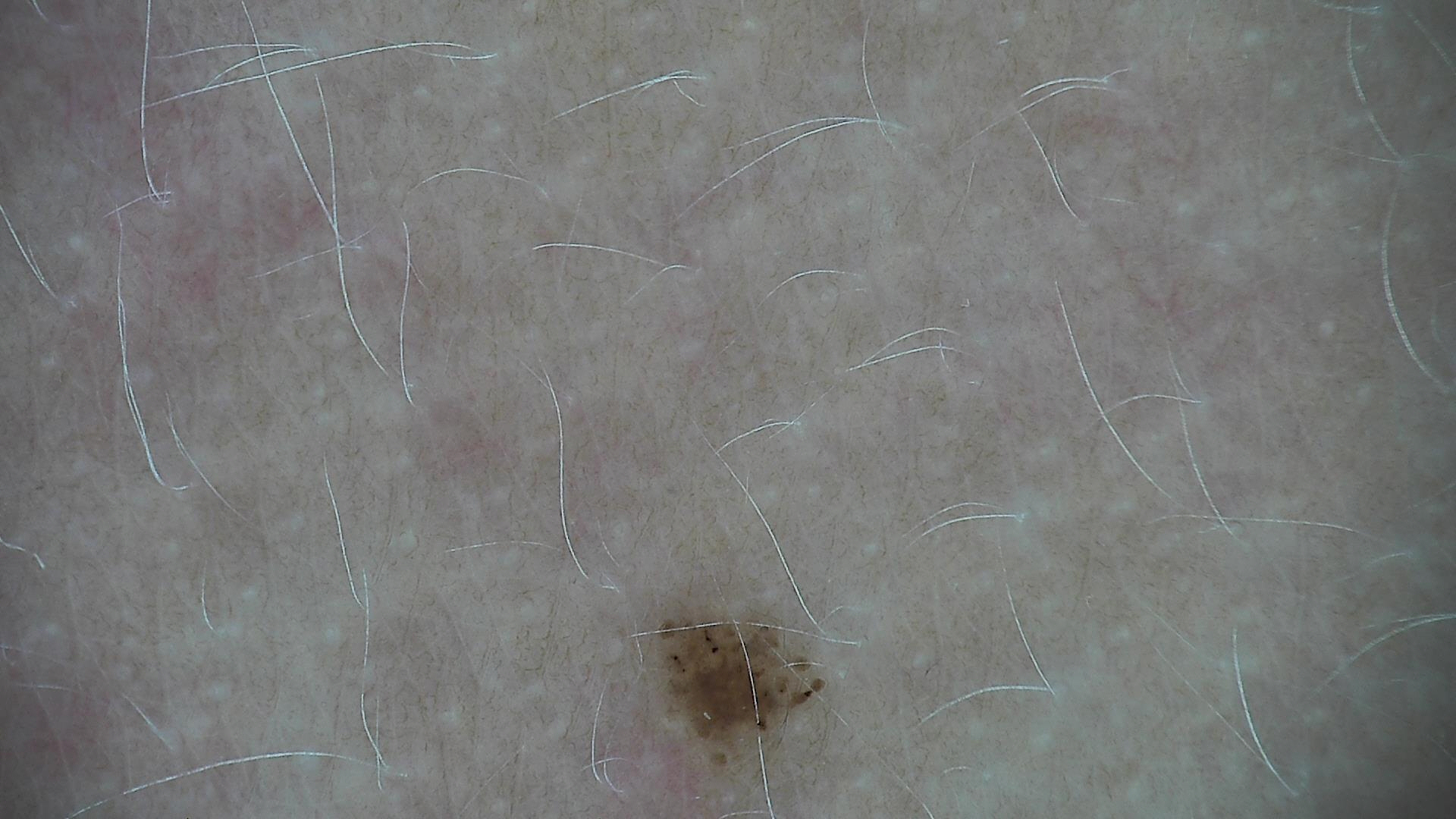modality = dermatoscopy | diagnostic label = dysplastic junctional nevus (expert consensus).